A dermatoscopic image of a skin lesion.
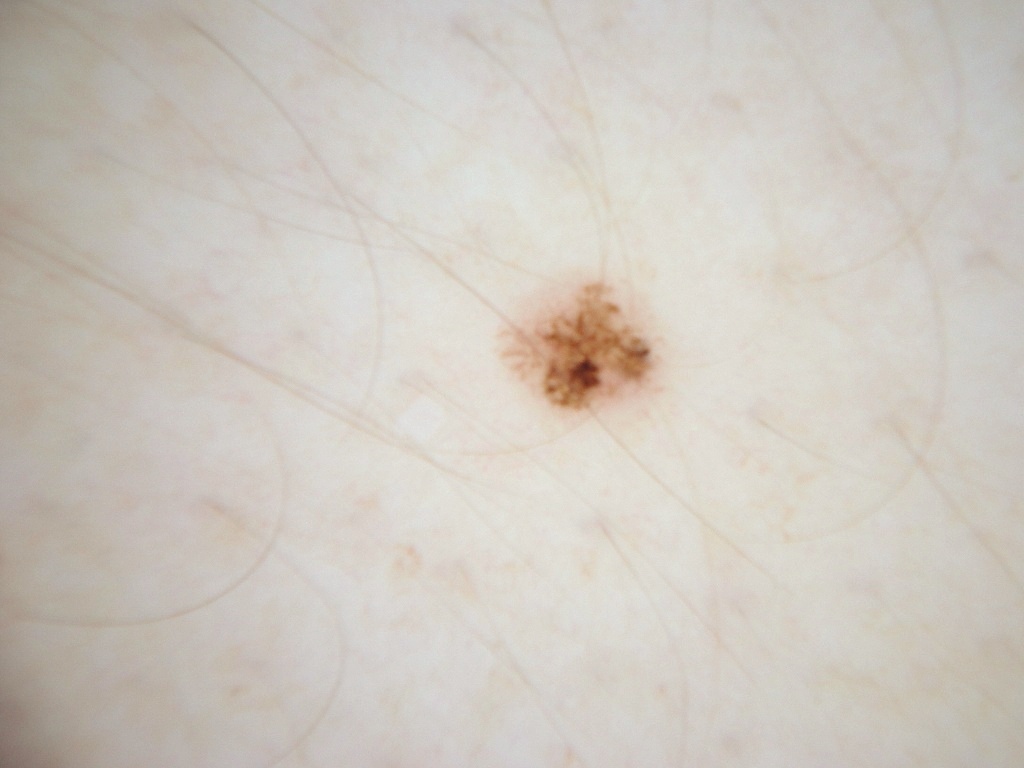bounding box=[504, 278, 659, 413]
absent dermoscopic findings=globules and streaks
assessment=a benign lesion